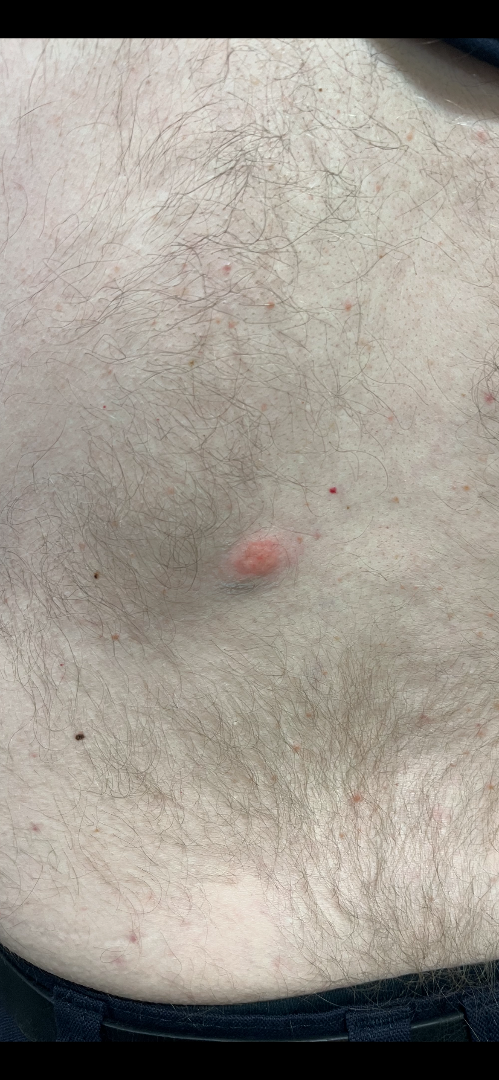Review:
The skin findings could not be characterized from the image.
Patient information:
Reported lesion symptoms include bothersome appearance and itching. The photo was captured at an angle. Located on the back of the torso. The patient is a male aged 50–59. The patient described the issue as a rash. The patient indicates the condition has been present for about one day.